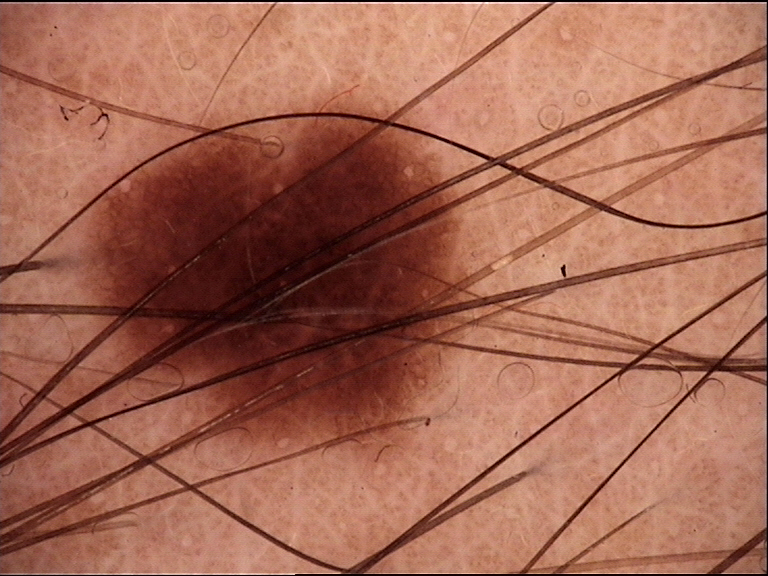modality = dermatoscopy | category = banal | class = junctional nevus (expert consensus).